A close-up photograph; texture is reported as raised or bumpy; the arm is involved:
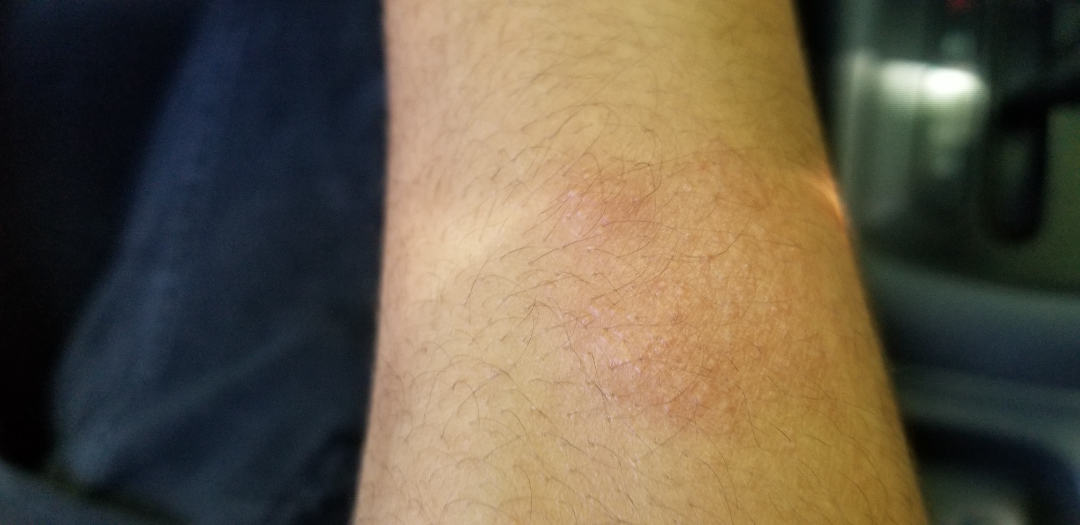The image was not sufficient for the reviewer to characterize the skin condition.